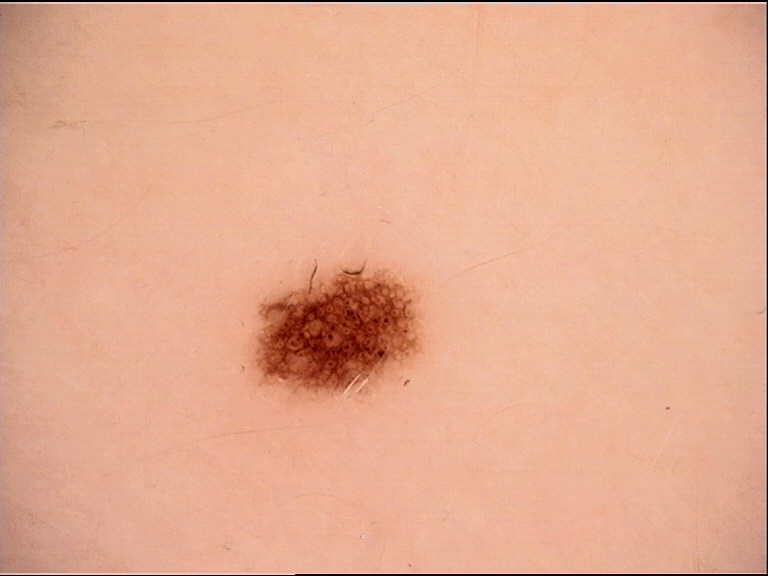Diagnosed as a junctional nevus.